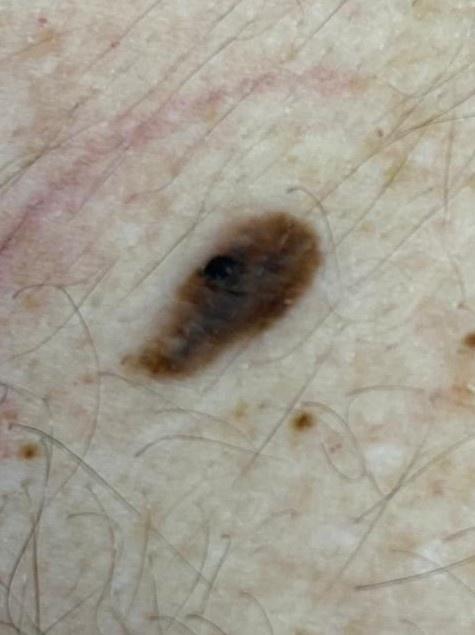Q: What is the diagnosis?
A: Melanoma (biopsy-proven)